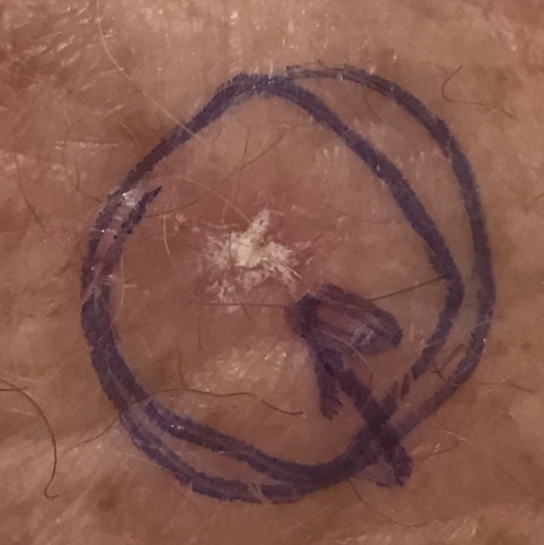Clinically diagnosed as an actinic keratosis.